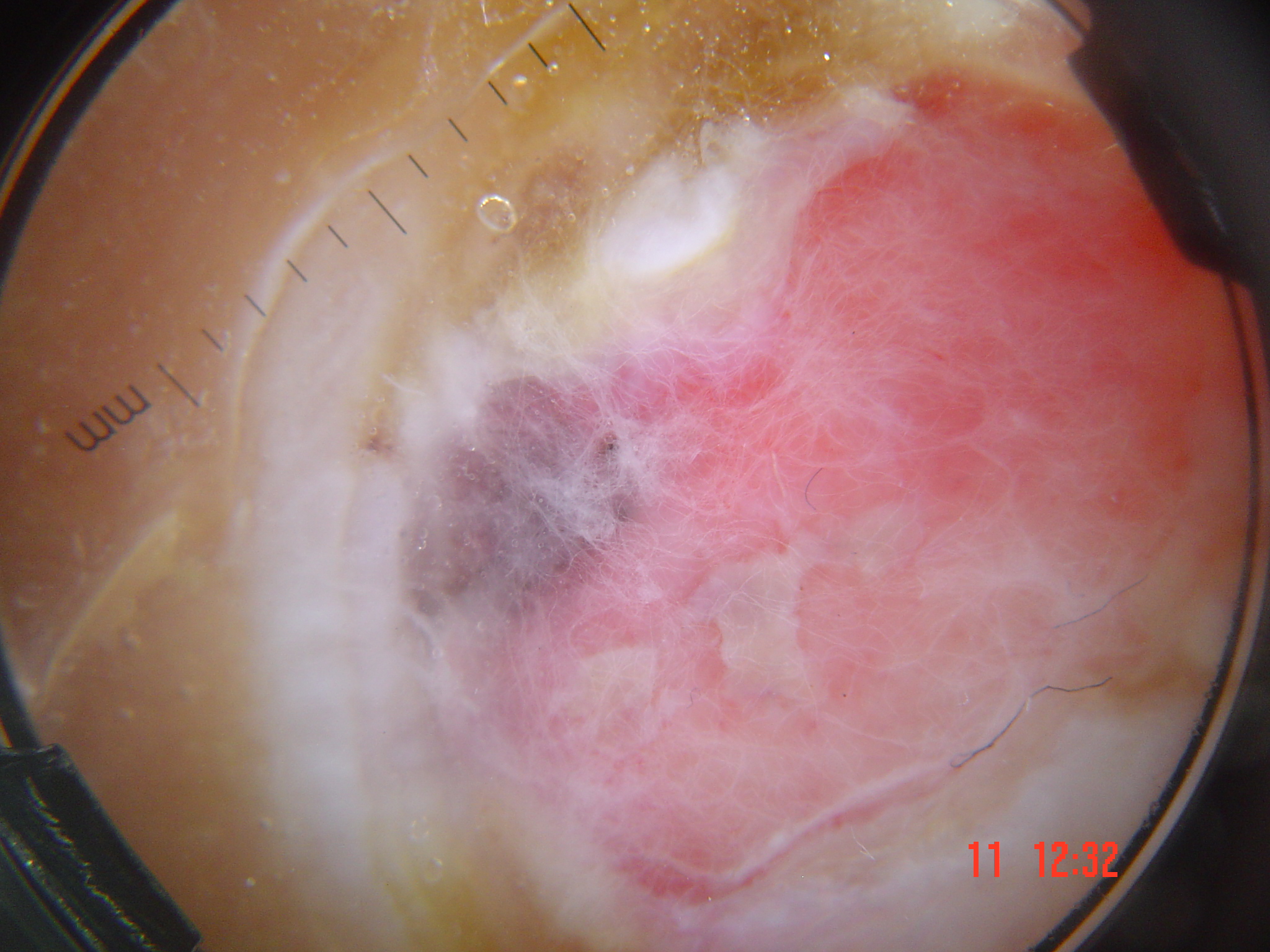A dermatoscopic image of a skin lesion.
Histopathologically confirmed as an acral nodular melanoma.